Reported duration is less than one week; the patient described the issue as a rash; the patient indicates the lesion is rough or flaky and raised or bumpy; this image was taken at an angle; the lesion is associated with itching — 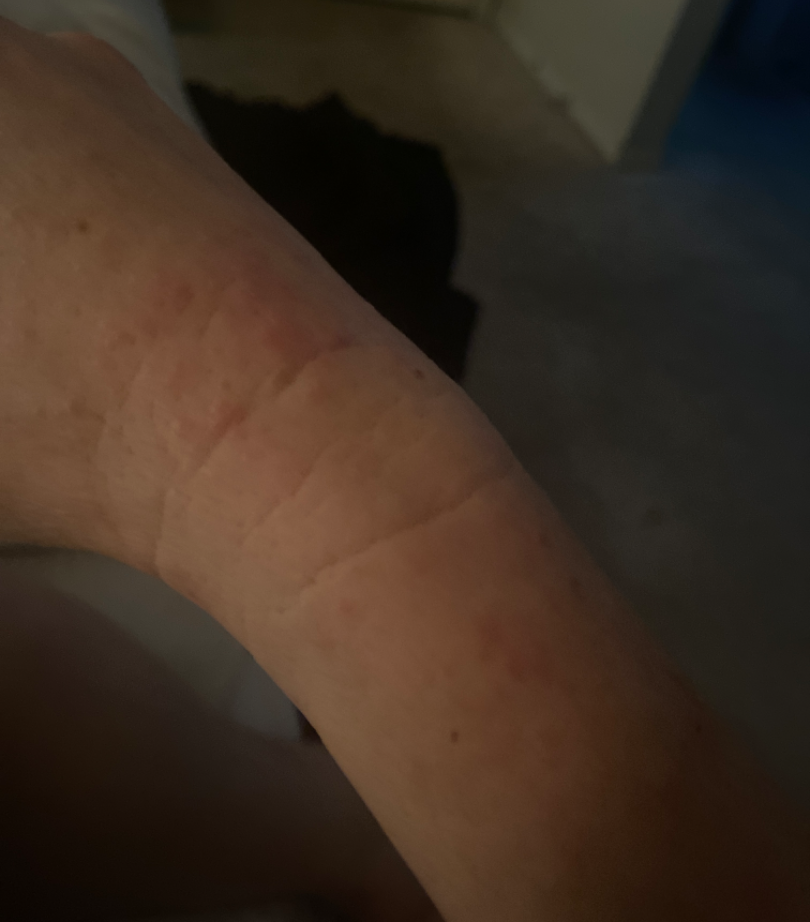assessment = indeterminate.